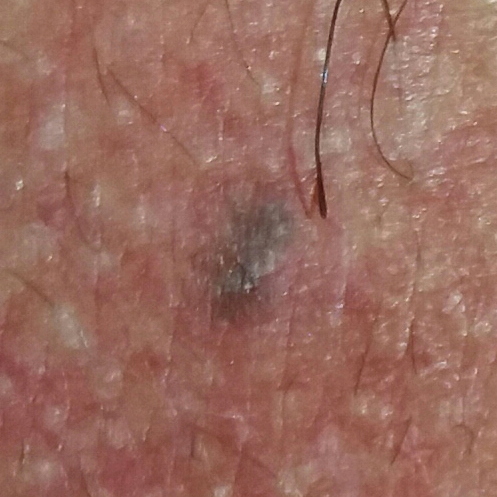{"patient": {"age": 40}, "image": "smartphone clinical photo", "symptoms": {"present": ["elevation", "growth"]}, "diagnosis": {"name": "nevus", "code": "NEV", "malignancy": "benign", "confirmation": "clinical consensus"}}